A dermoscopy image of a single skin lesion:
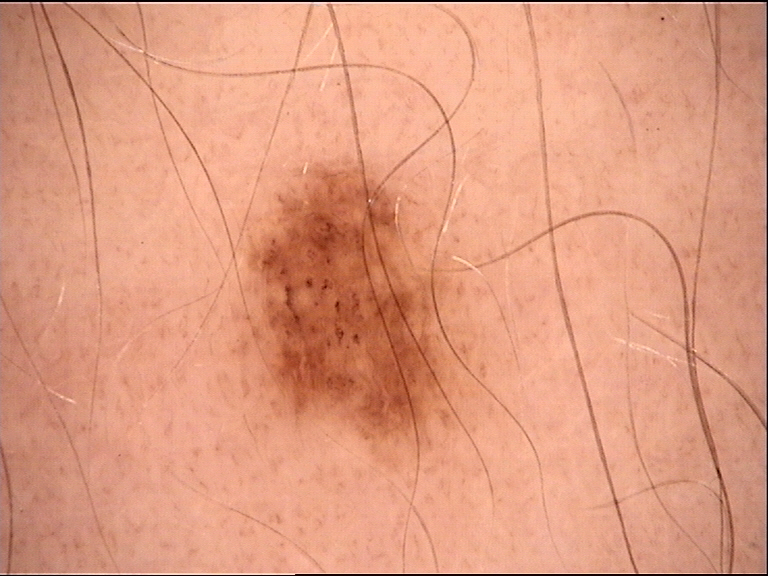Q: How is the lesion classified?
A: banal
Q: What is this lesion?
A: junctional nevus (expert consensus)